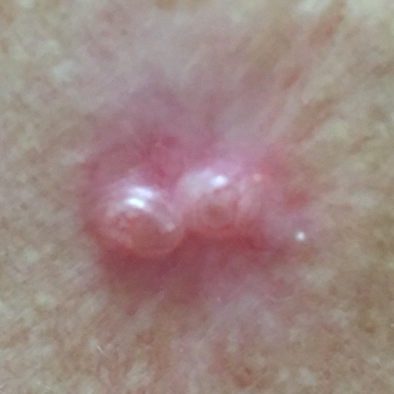{"skin_type": "I", "image": "clinical photograph", "patient": {"age": 51, "gender": "female"}, "risk_factors": {"positive": ["prior cancer (patient or family)"]}, "lesion_location": "the chest", "lesion_size": {"diameter_1_mm": 11.0, "diameter_2_mm": 6.0}, "diagnosis": {"name": "basal cell carcinoma", "code": "BCC", "malignancy": "malignant", "confirmation": "histopathology"}}